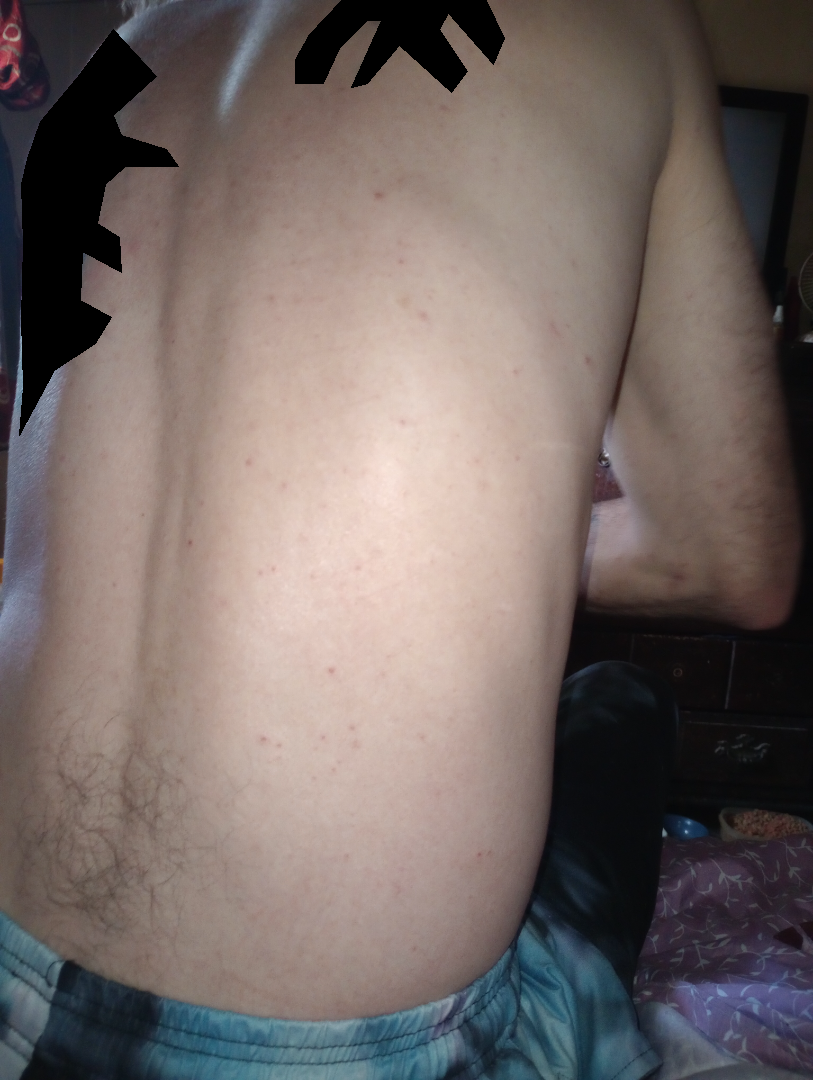framing — at a distance | differential diagnosis — reviewed remotely by one dermatologist: the impression was split between Acne and Folliculitis; a remote consideration is Scabies.